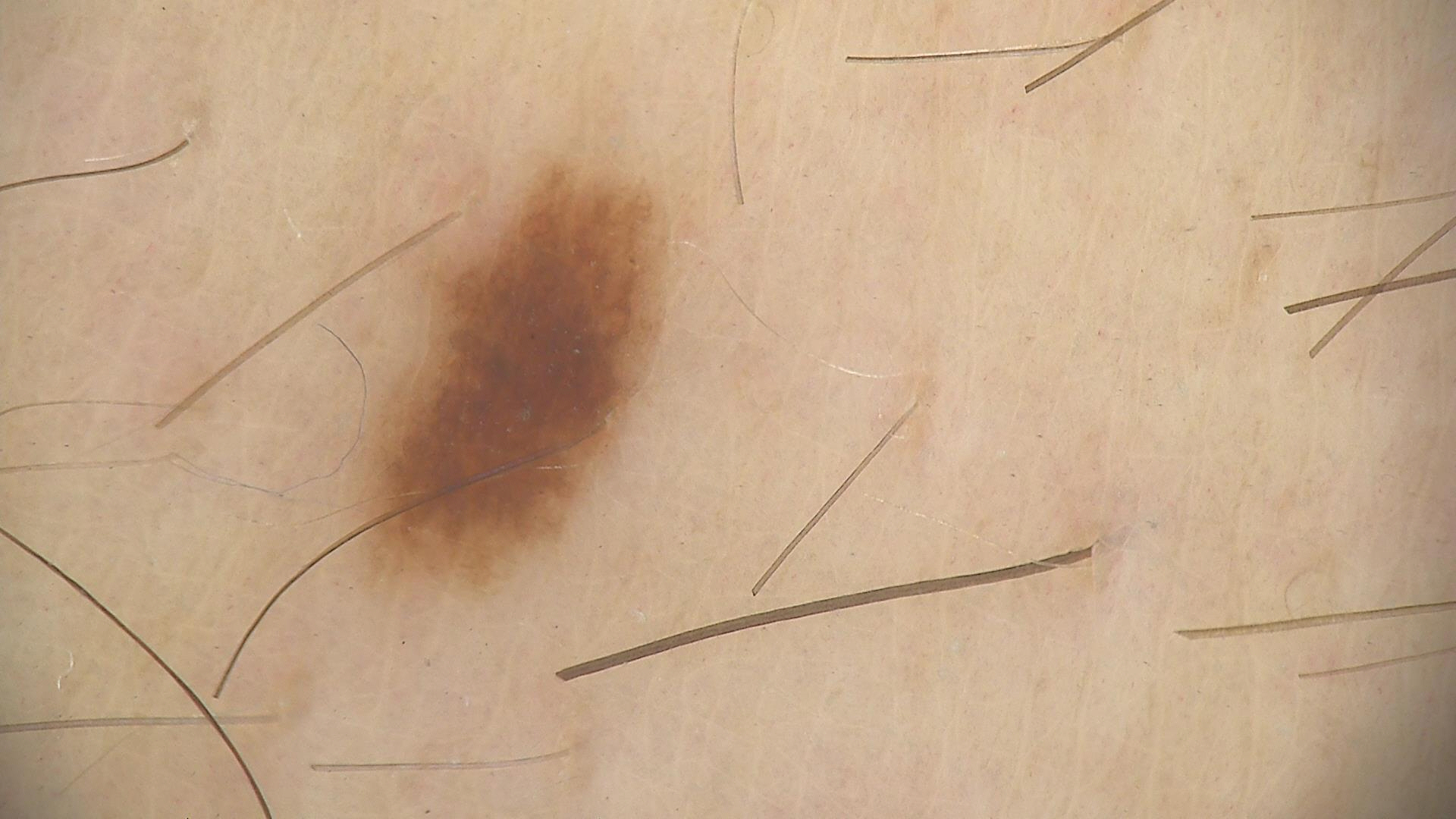  diagnosis:
    name: junctional nevus
    code: jb
    malignancy: benign
    super_class: melanocytic
    confirmation: expert consensus